A dermoscopy image of a single skin lesion.
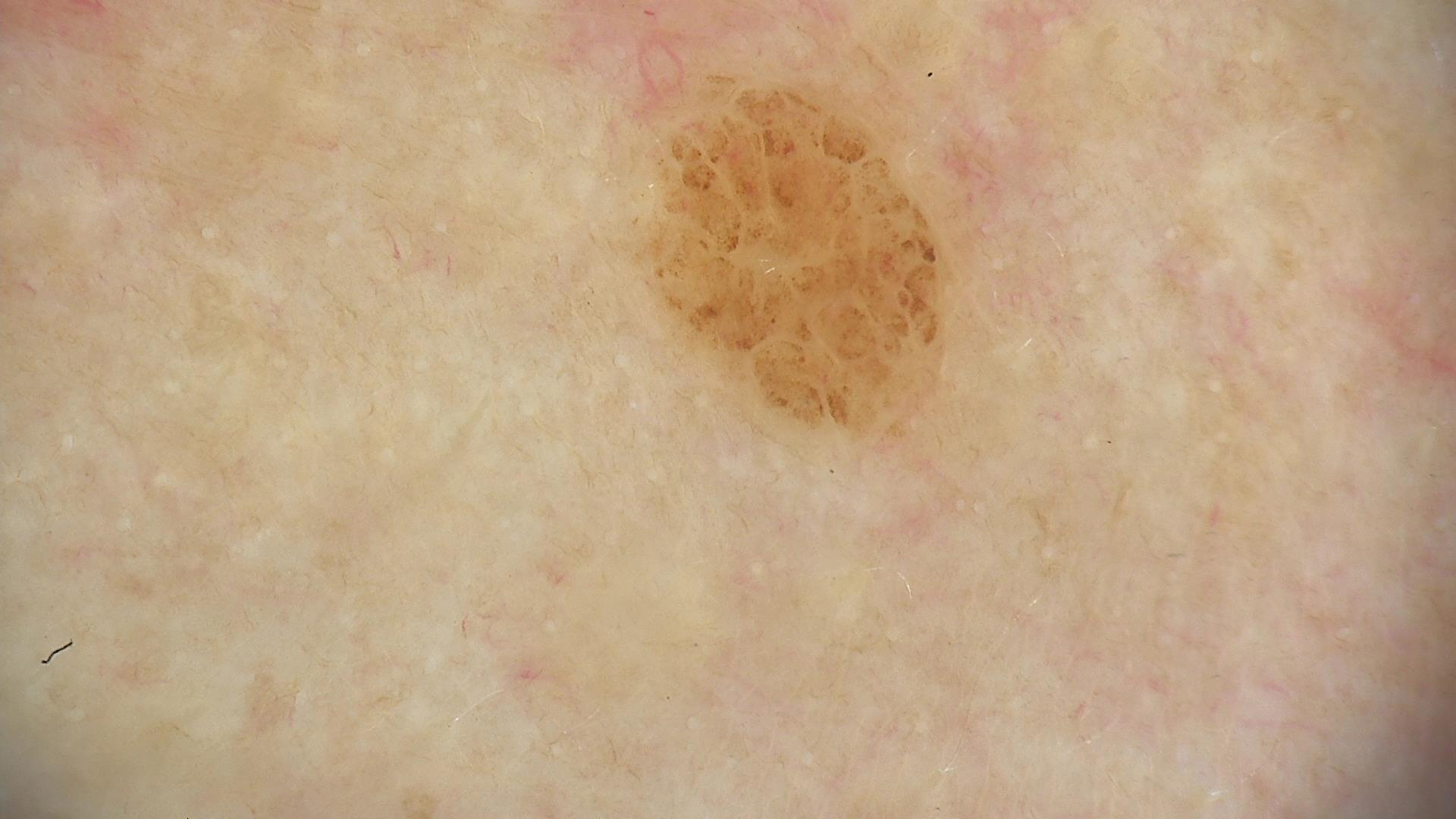category=banal
diagnosis=compound nevus (expert consensus)